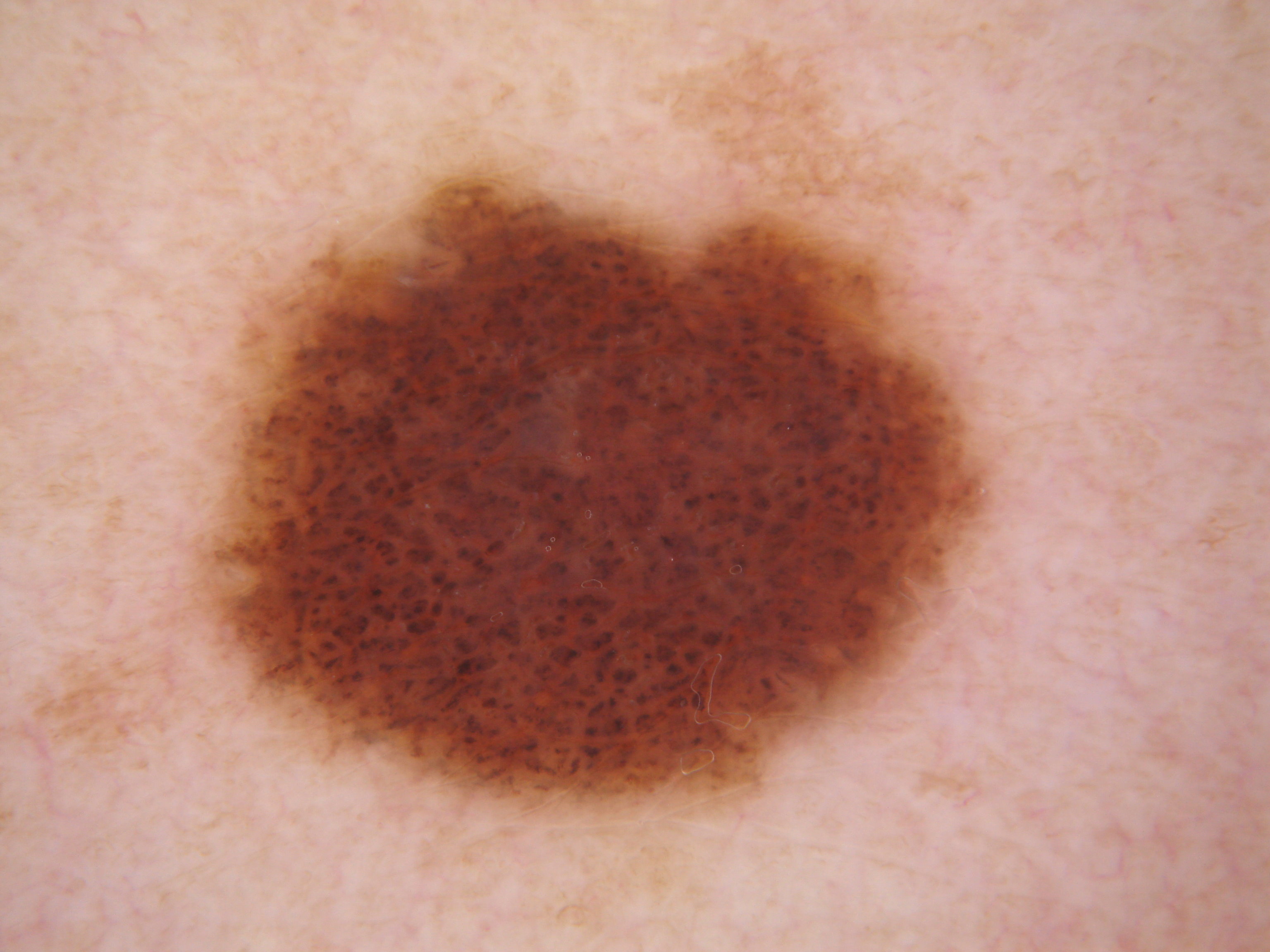modality — dermoscopic image; lesion location — <bbox>192, 169, 993, 816</bbox>; impression — a melanocytic nevus, a benign lesion.